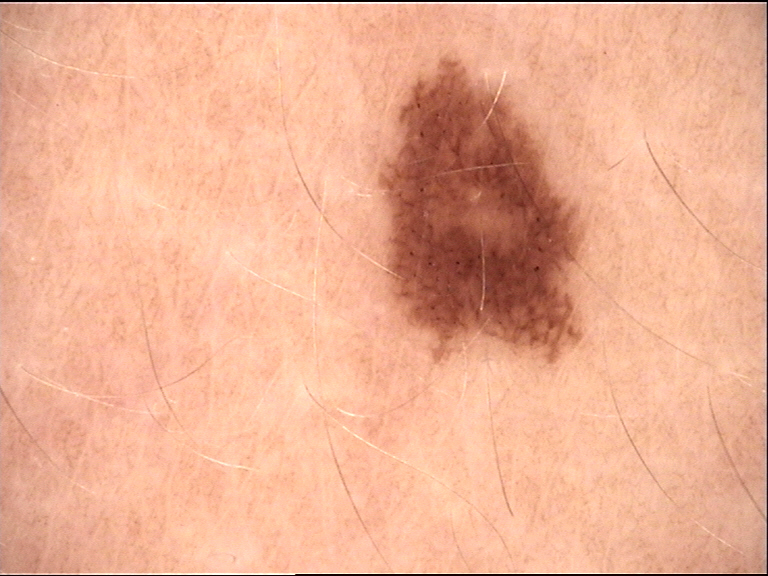| key | value |
|---|---|
| label | junctional nevus (expert consensus) |